The lesion is associated with enlargement, bothersome appearance, burning, pain and itching. The photograph is a close-up of the affected area. The lesion is described as raised or bumpy and fluid-filled. The affected area is the back of the torso and front of the torso. The patient indicates the condition has been present for less than one week. The patient considered this a rash: 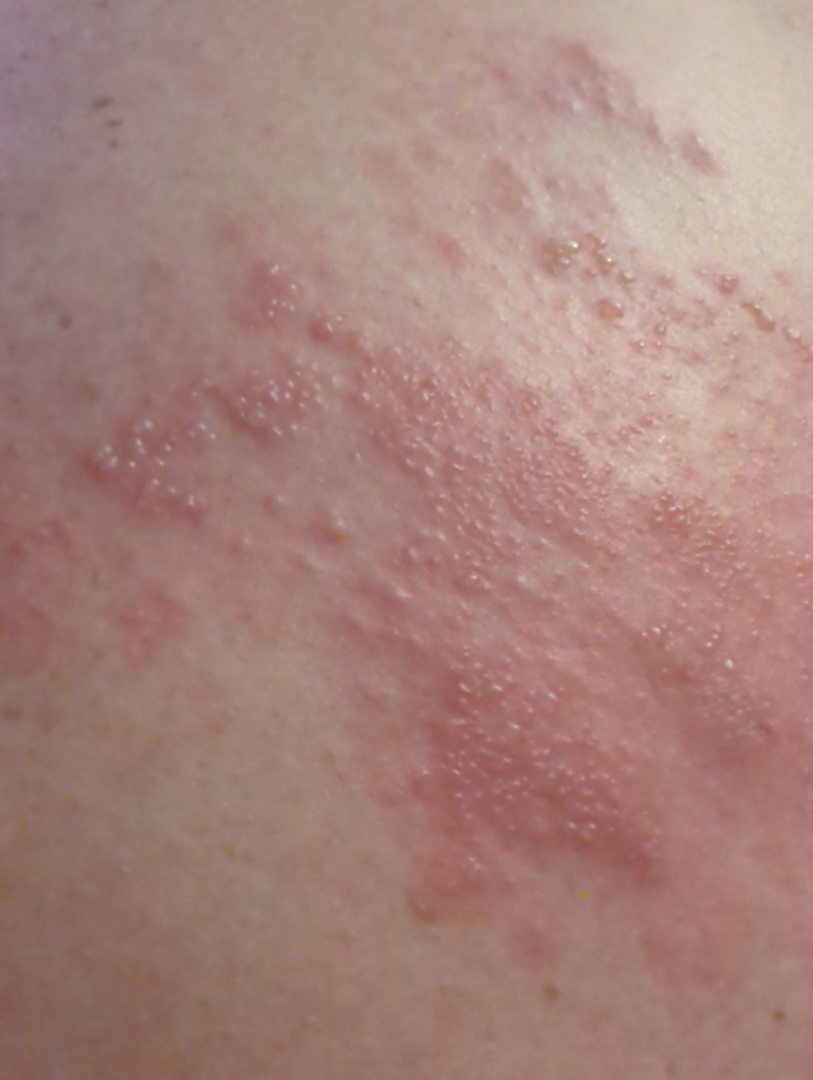{"differential": {"tied_lead": ["Herpes Zoster", "Allergic Contact Dermatitis"]}}